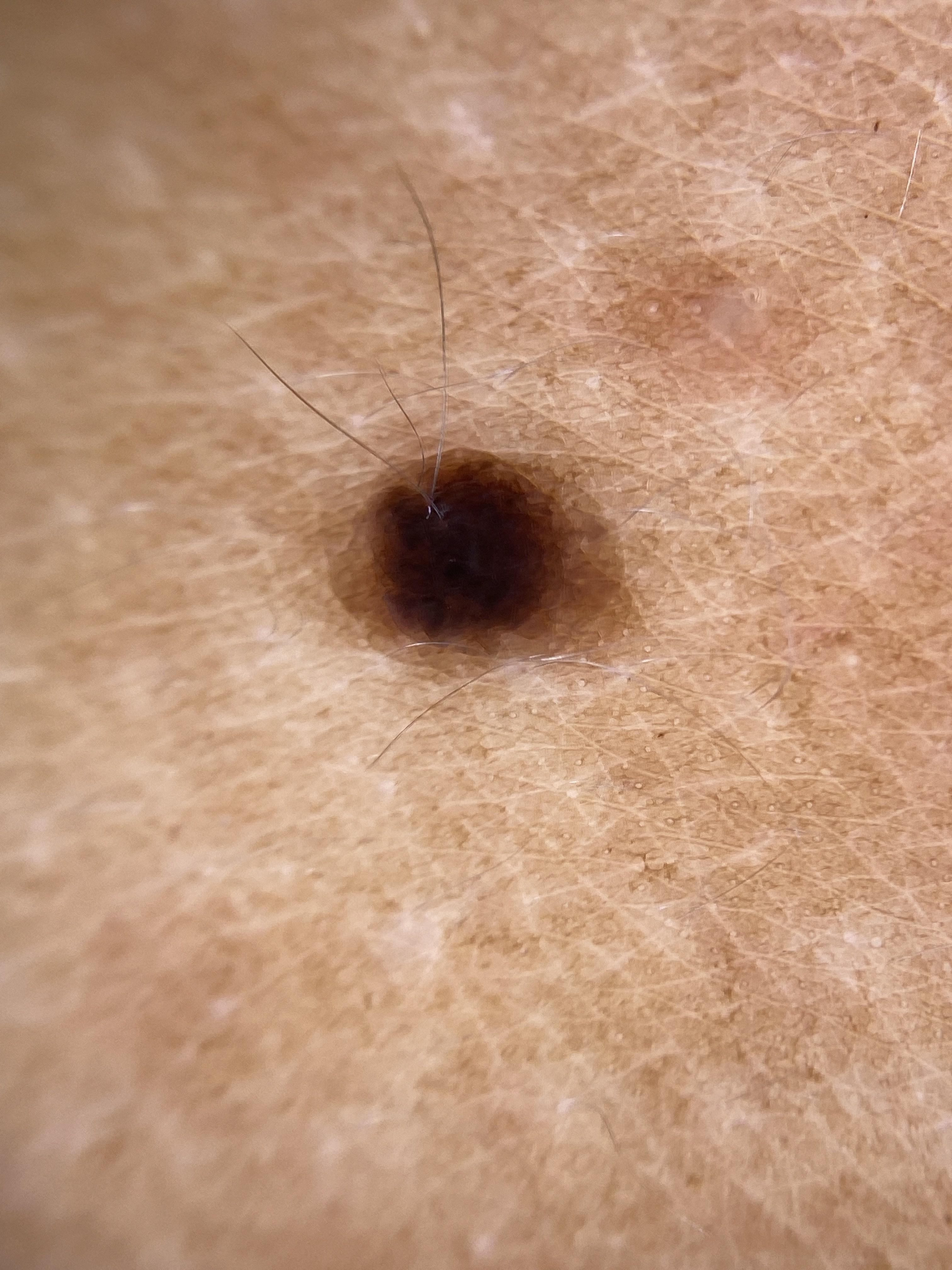A dermoscopy image of a single skin lesion.
A female subject aged approximately 35.
The lesion is on an upper extremity.
Expert review favored a nevus.